A dermoscopic photograph of a skin lesion:
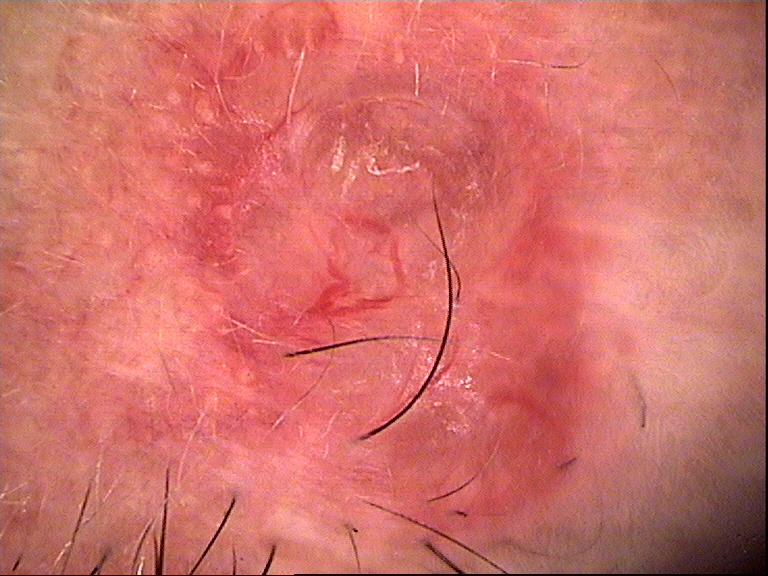Histopathologically confirmed as a basal cell carcinoma.